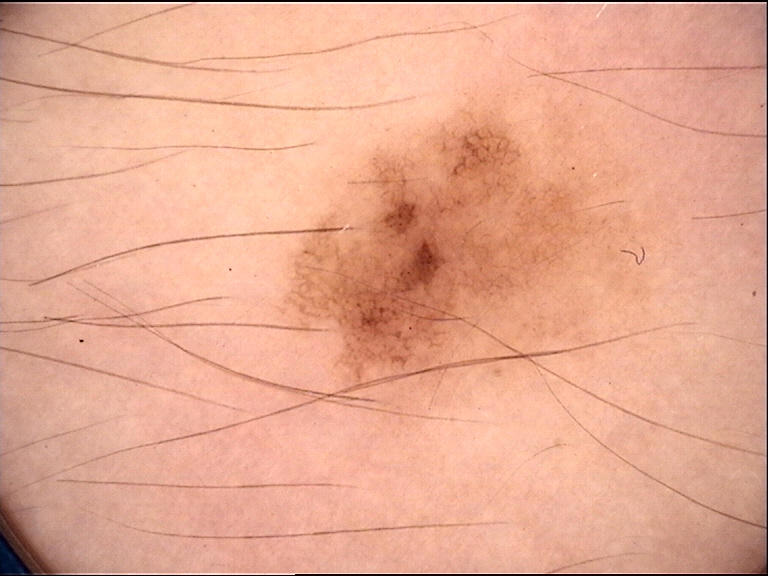A dermoscopic close-up of a skin lesion.
The diagnostic label was a congenital junctional nevus.